Dermoscopy of a skin lesion:
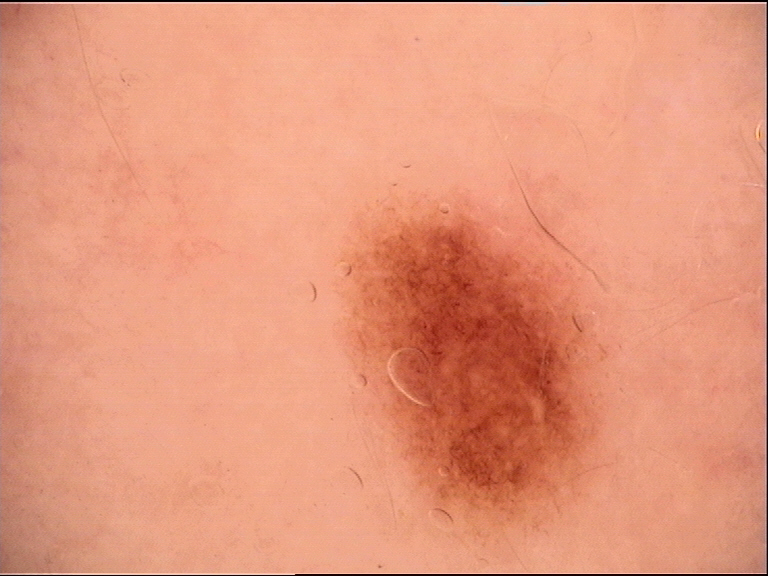{"diagnosis": {"name": "dysplastic junctional nevus", "code": "jd", "malignancy": "benign", "super_class": "melanocytic", "confirmation": "expert consensus"}}